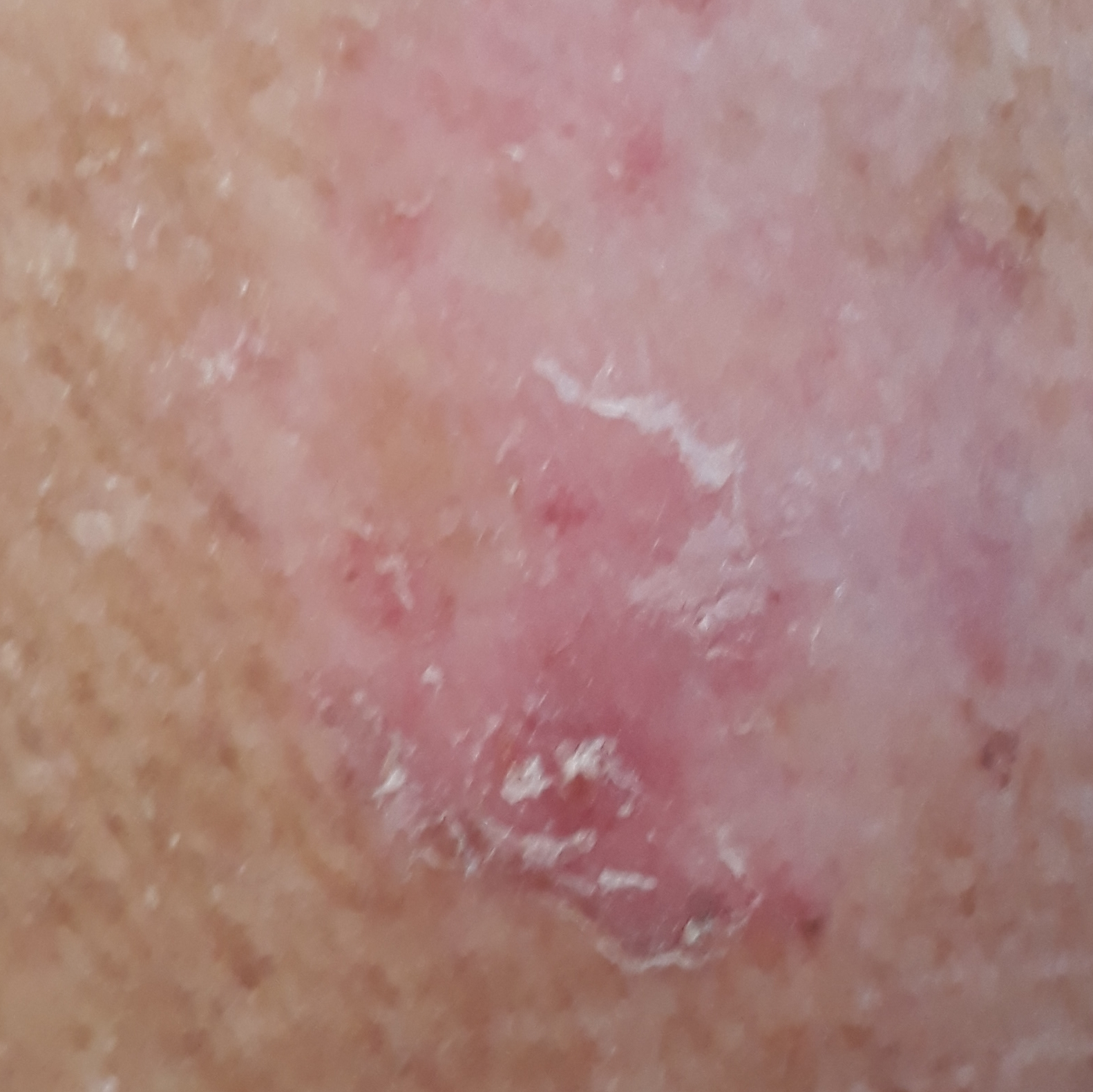skin phototype: III; imaging: smartphone clinical photo; subject: female, in their early 70s; body site: an arm; lesion size: 10x6 mm; symptoms: change in appearance, itching, growth; assessment: actinic keratosis (clinical consensus).